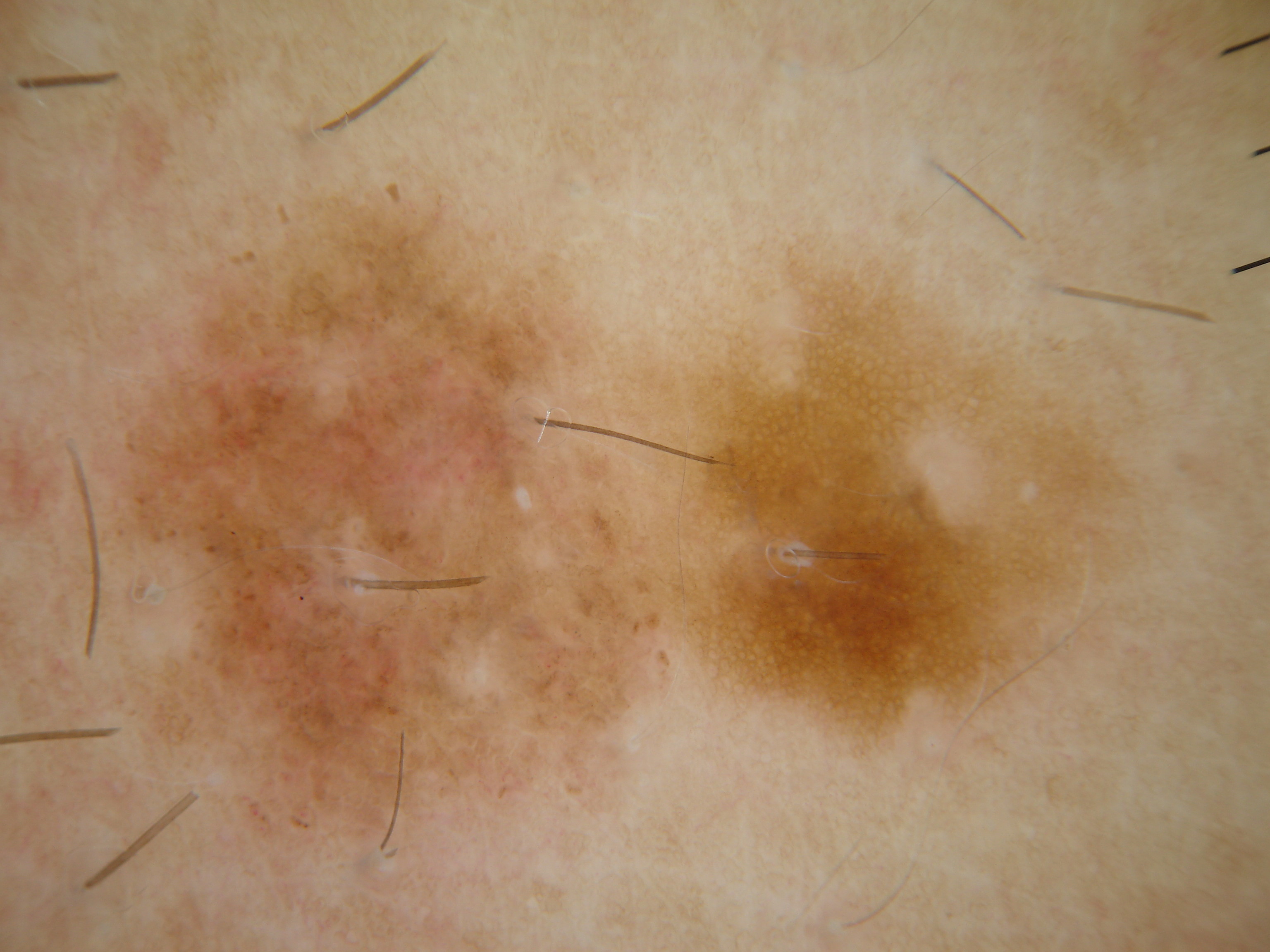A skin lesion imaged with a dermatoscope.
In (x1, y1, x2, y2) order, the lesion is located at 92, 161, 684, 877.
The lesion takes up a moderate portion of the field.
Dermoscopic examination shows globules, with no streaks.
The diagnostic assessment was a benign skin lesion.